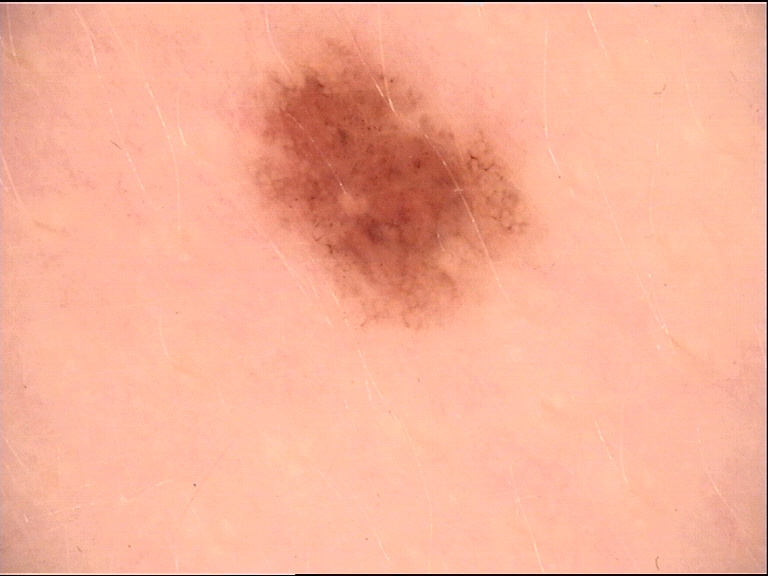Classified as a dysplastic junctional nevus.